Dermoscopy of a skin lesion: 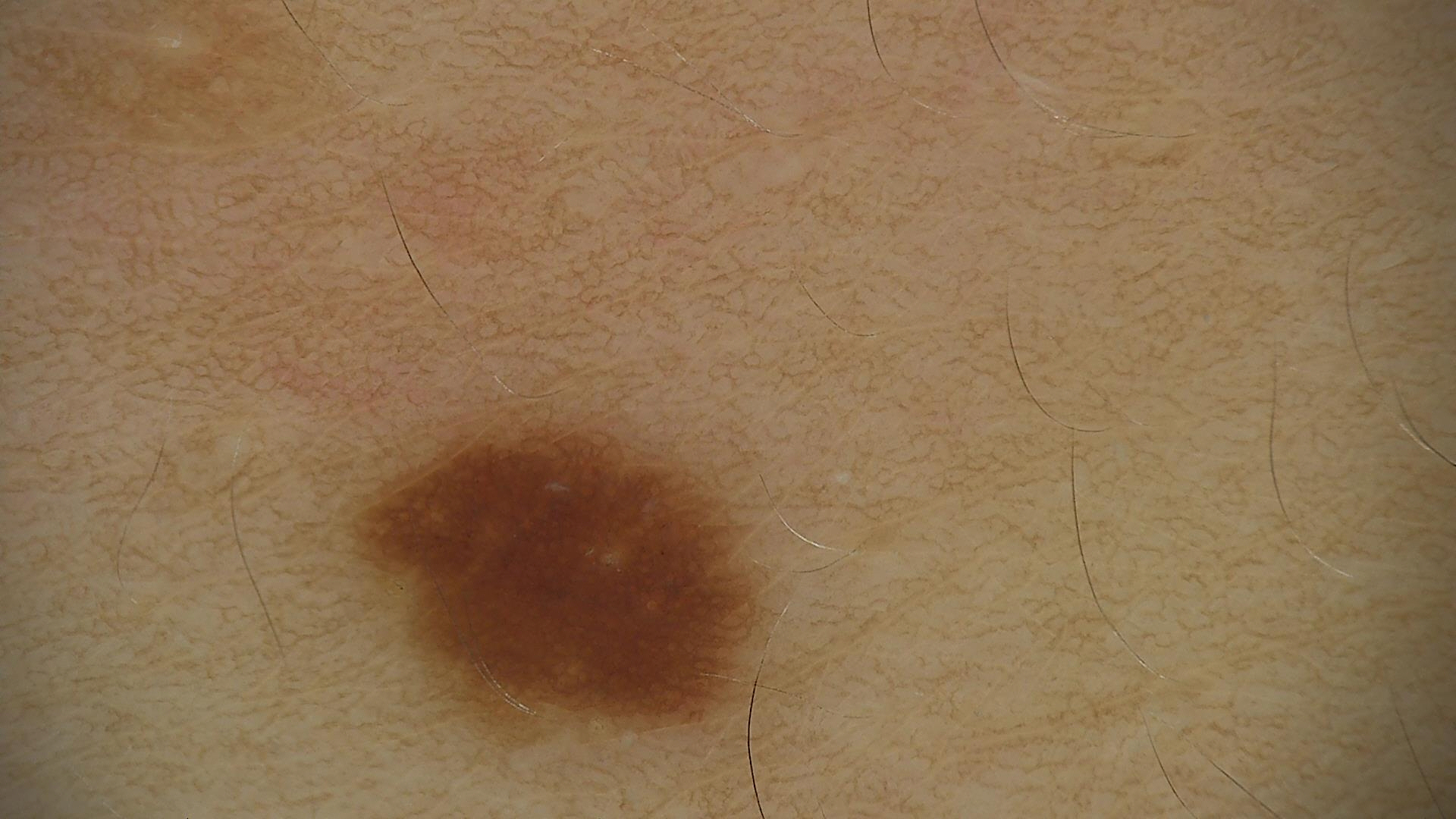{"diagnosis": {"name": "dysplastic junctional nevus", "code": "jd", "malignancy": "benign", "super_class": "melanocytic", "confirmation": "expert consensus"}}